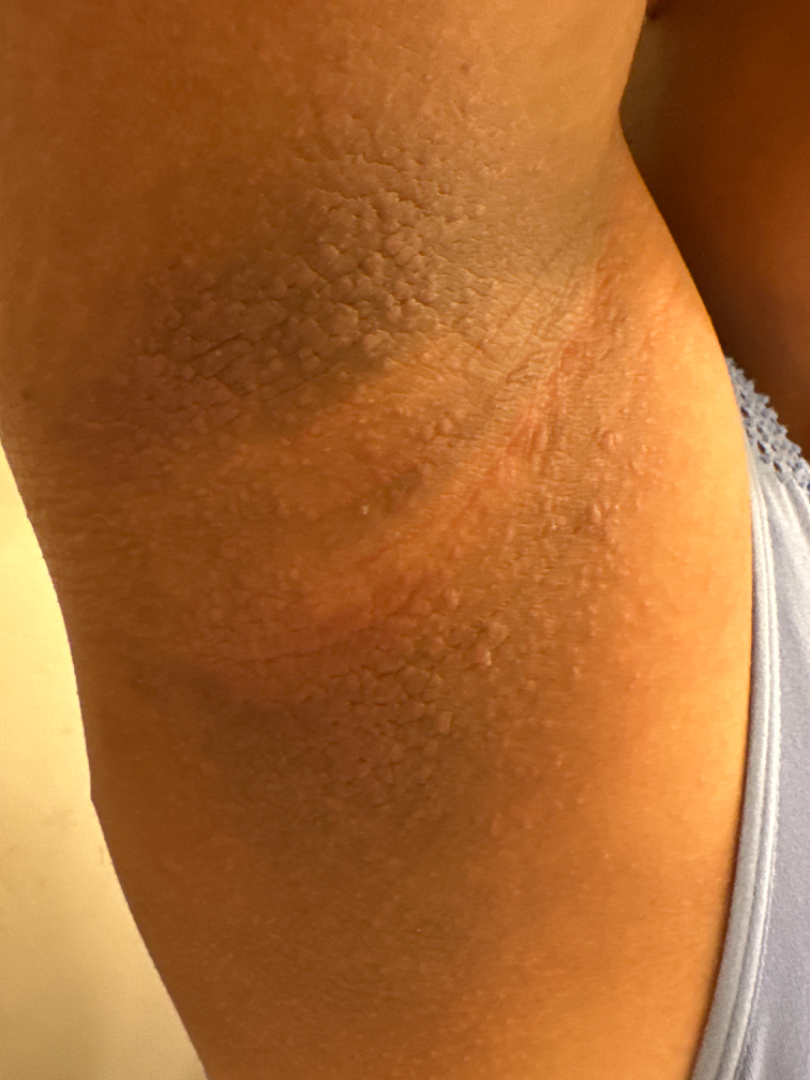• patient-reported symptoms — bothersome appearance, pain, itching, burning and enlargement
• image framing — close-up
• described texture — raised or bumpy and rough or flaky
• symptom duration — less than one week
• differential diagnosis — the reviewer's impression was Acanthosis nigricans